A male patient in their 80s; a wide-field clinical photograph of a skin lesion — 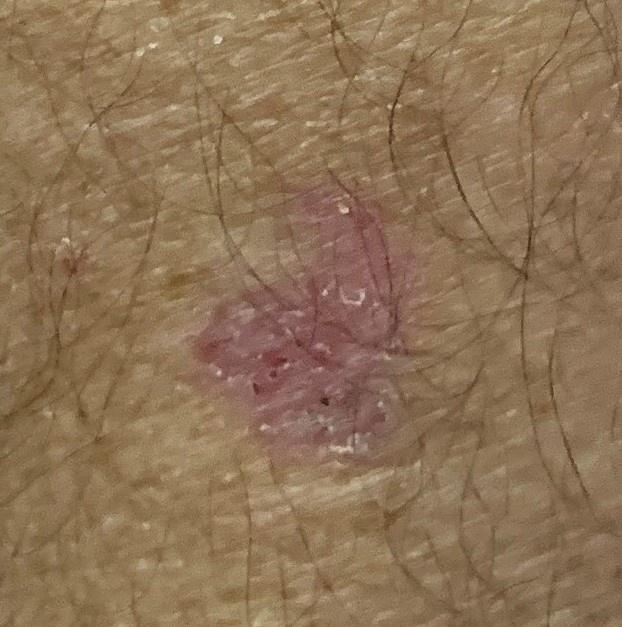Summary:
The lesion involves an upper extremity.
Conclusion:
Histopathologically confirmed as a basal cell carcinoma.